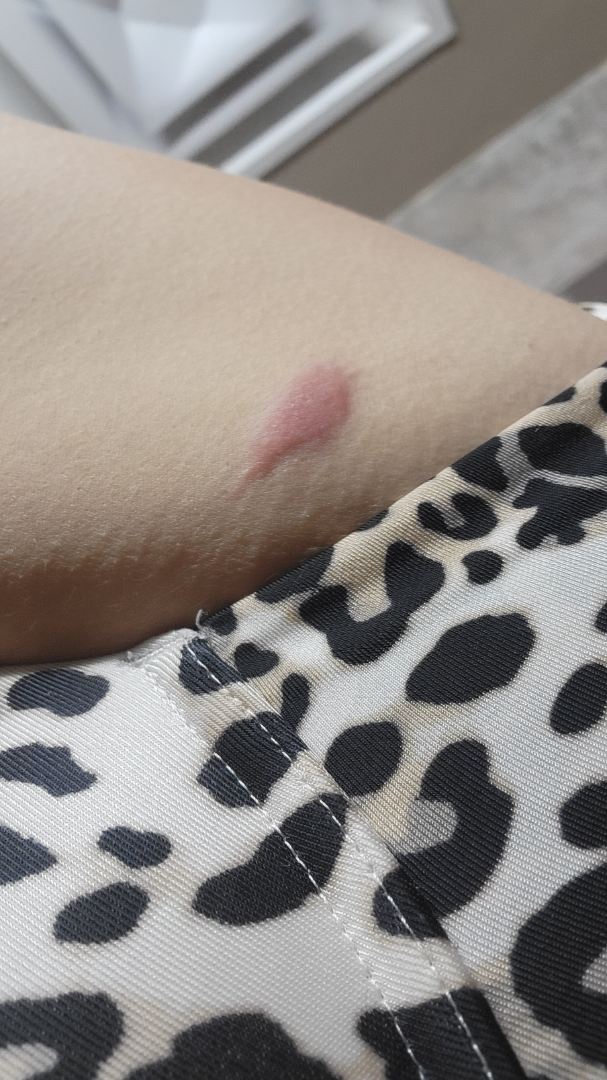assessment: unable to determine; texture: raised or bumpy; associated systemic symptoms: joint pain, shortness of breath and fatigue; view: at a distance; symptoms: itching and burning.